Close-up view. The back of the hand is involved.
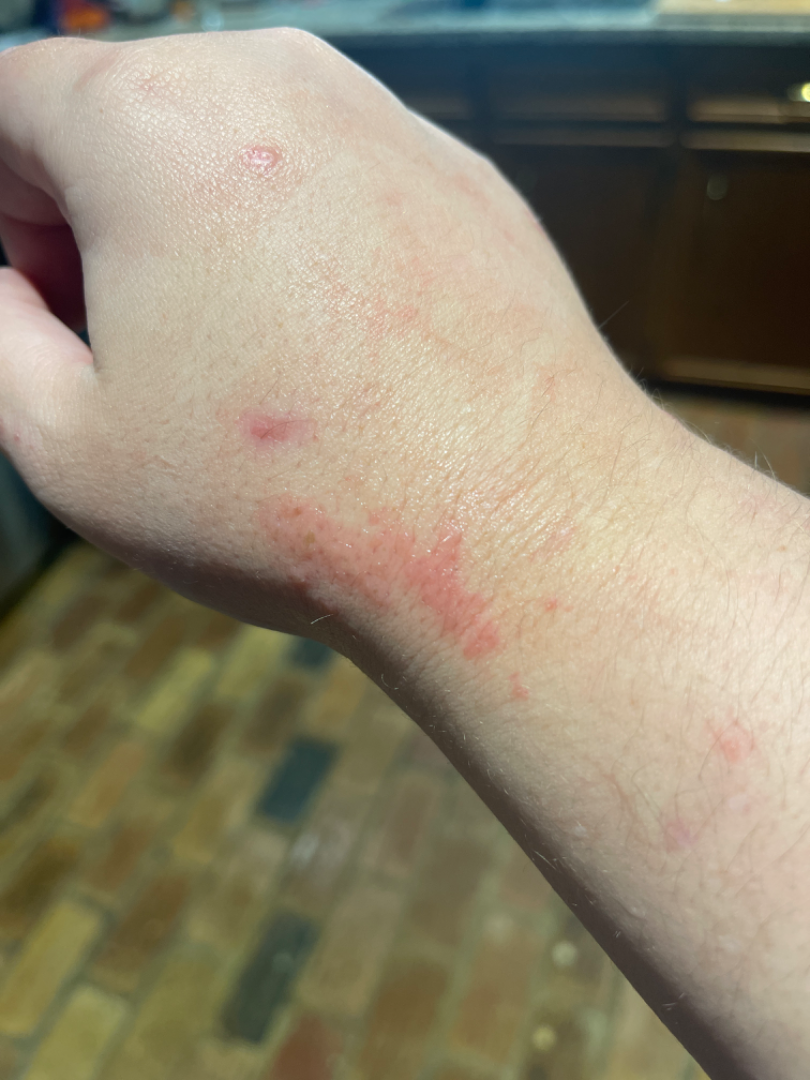Findings:
• patient's own categorization: a rash
• surface texture: raised or bumpy
• history: about one day
• differential diagnosis: the leading consideration is Allergic Contact Dermatitis; also raised was Urticaria; possibly Irritant Contact Dermatitis